Close-up view · Fitzpatrick skin type IV; human graders estimated Monk Skin Tone 3 or 4 — 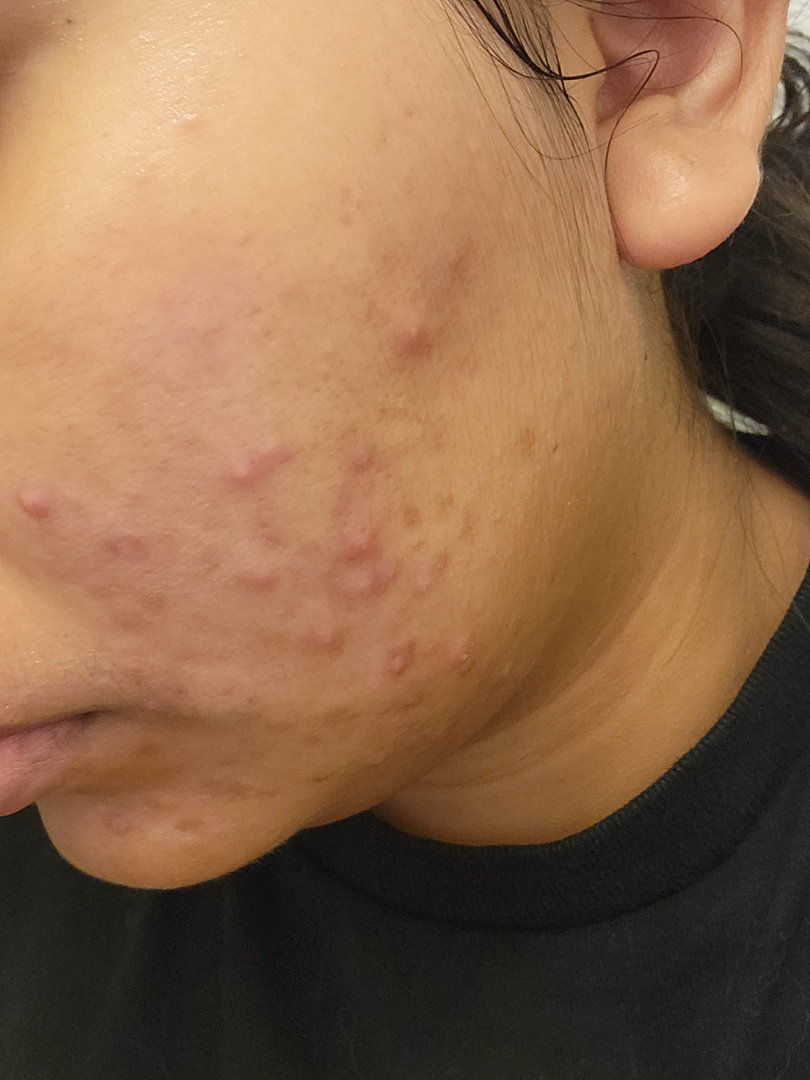Impression:
Acne (1.00).